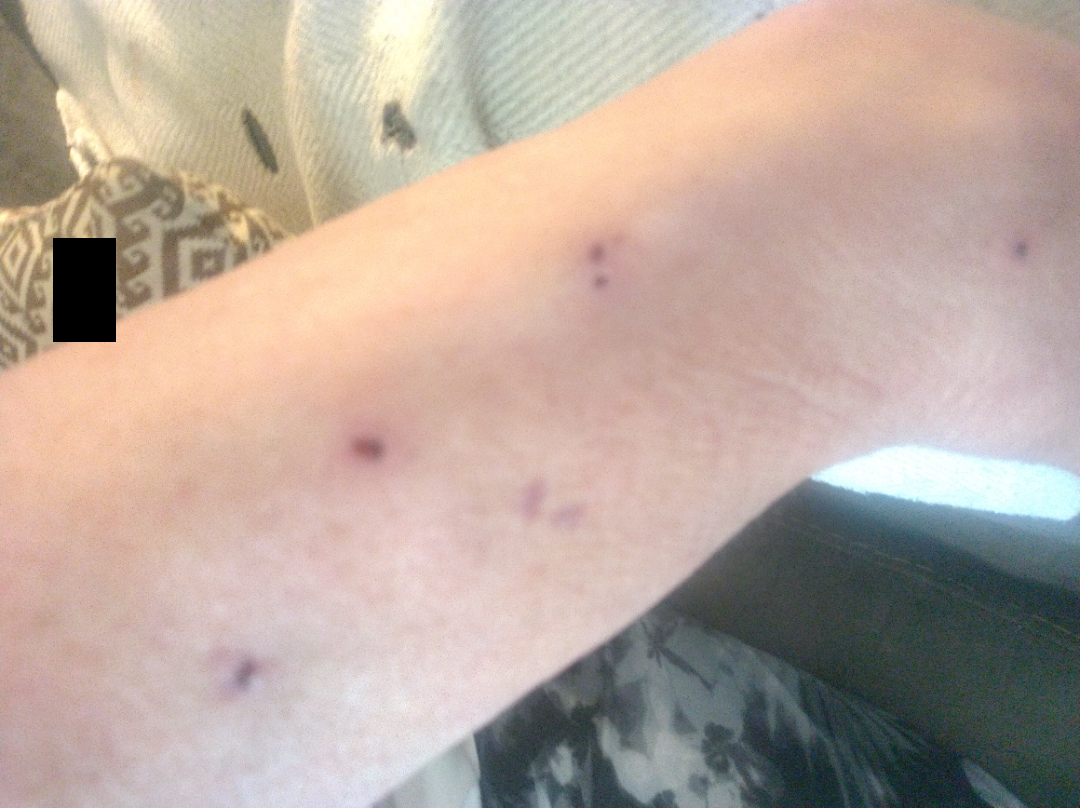The reviewer was unable to grade this case for skin condition.
The photograph is a close-up of the affected area.